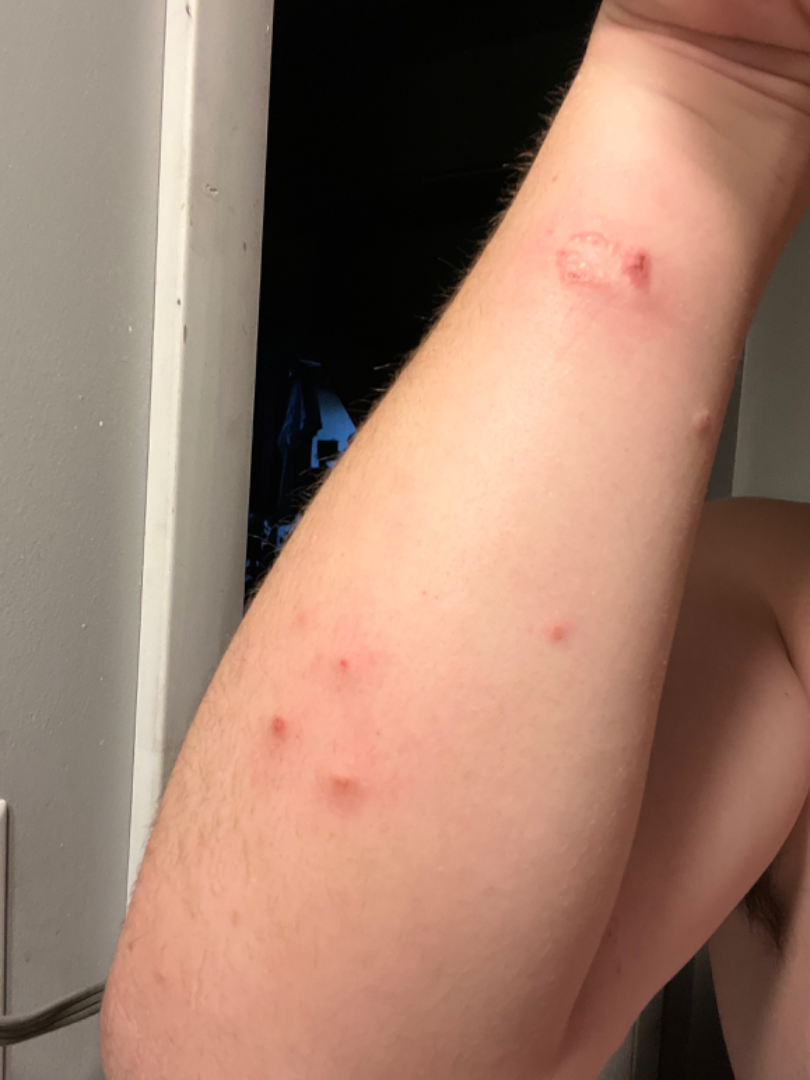  assessment: could not be assessed
  body_site:
    - arm
    - leg
  symptoms: itching
  texture: raised or bumpy
  patient: male, age 18–29
  shot_type: close-up